A dermoscopic photograph of a skin lesion.
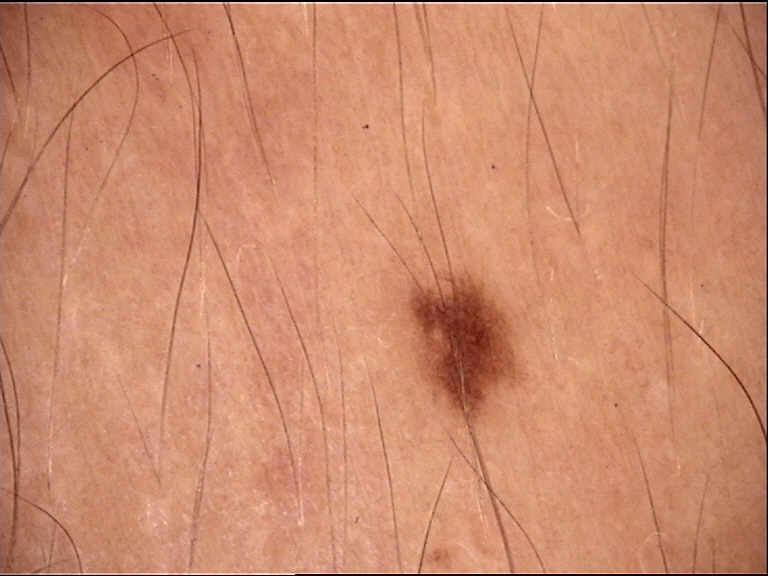Consistent with a dysplastic junctional nevus.